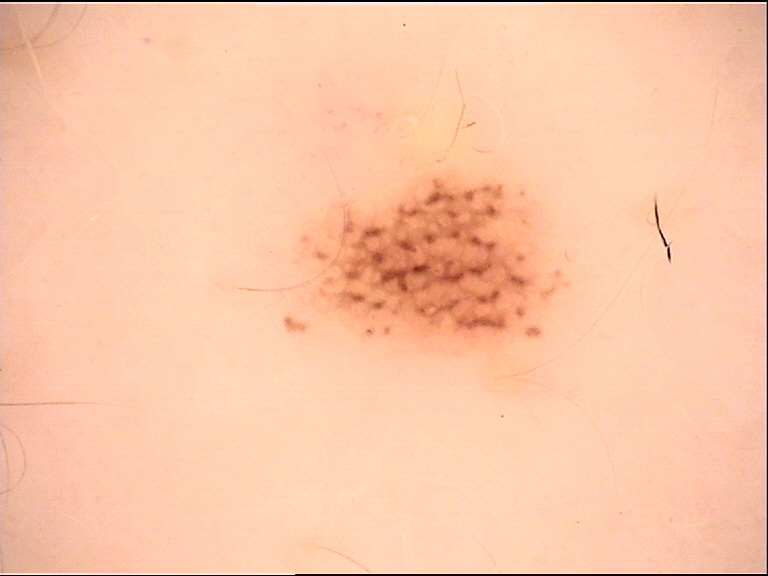Findings:
– modality: dermatoscopy
– label: dysplastic junctional nevus (expert consensus)